A male patient, approximately 65 years of age; a skin lesion imaged with a dermatoscope:
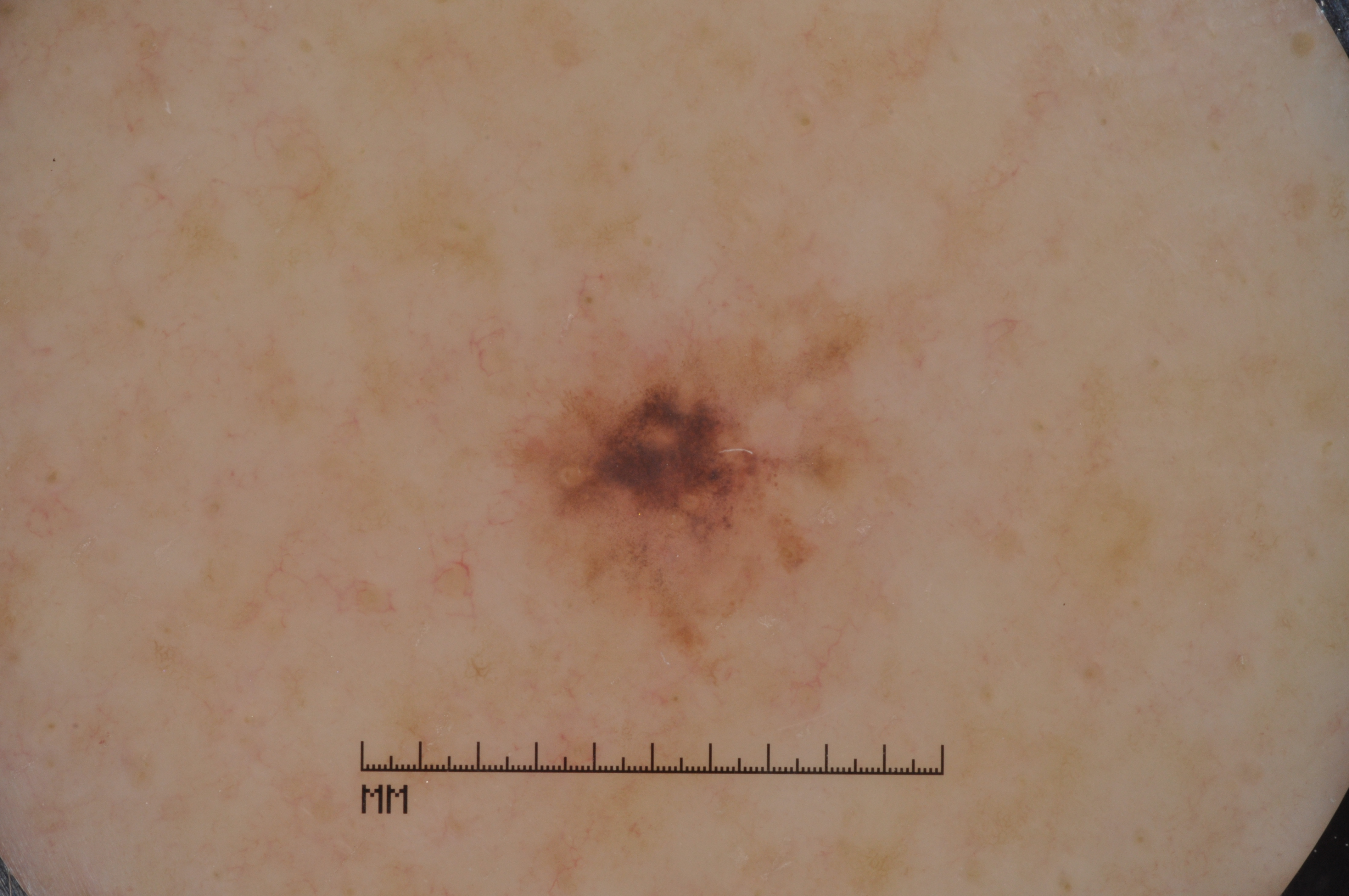Summary:
In (x1, y1, x2, y2) order, lesion location: 490, 274, 920, 702. Dermoscopy demonstrates pigment network and milia-like cysts, with no streaks or negative network. The lesion takes up about 10% of the image.
Conclusion:
Histopathologically confirmed as a melanoma.